A male patient, roughly 25 years of age. A dermoscopic view of a skin lesion: 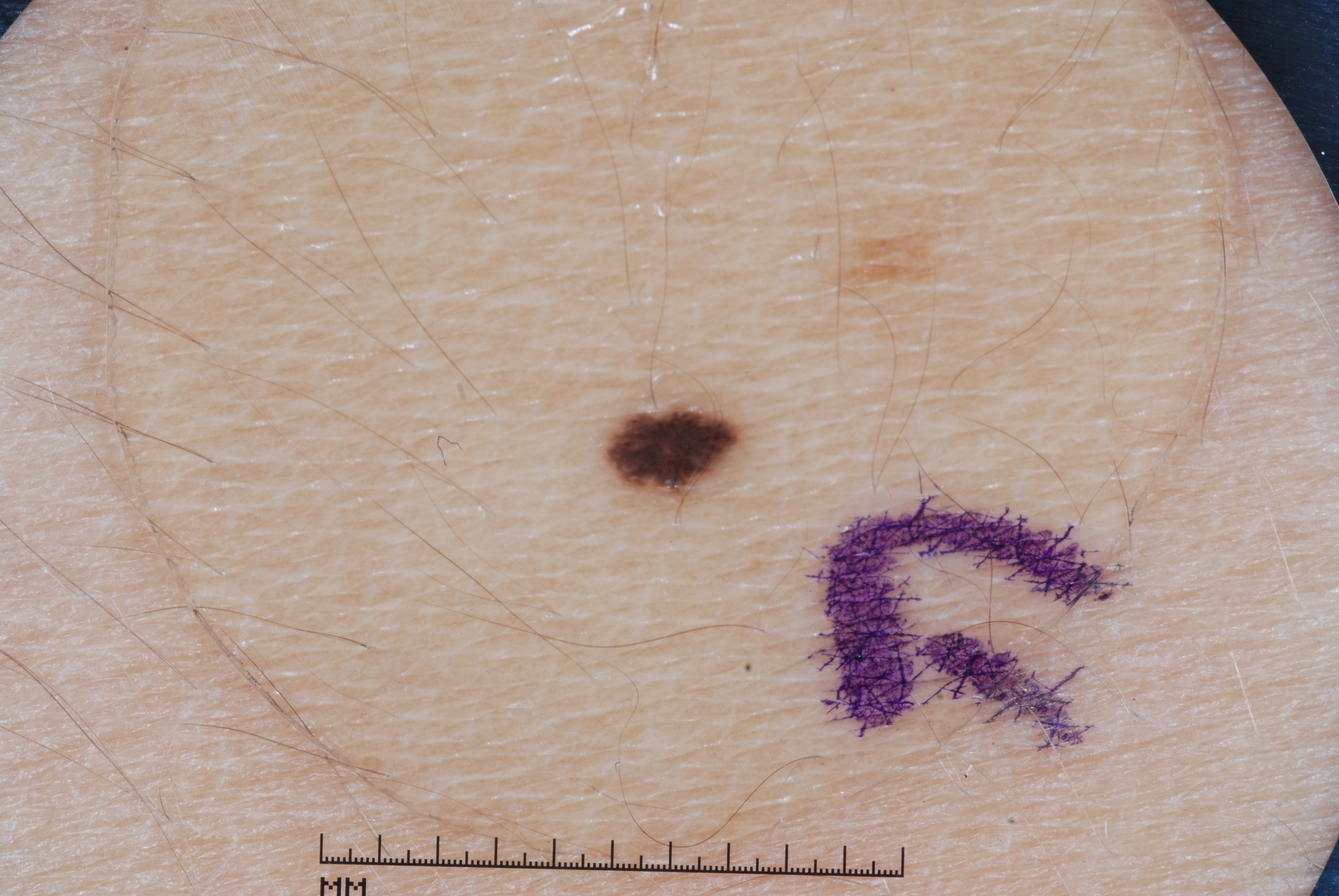lesion location: x1=617, y1=406, x2=742, y2=497 | features: streaks | diagnosis: a melanocytic nevus, a benign skin lesion.